A wide-field clinical photograph of a skin lesion; Fitzpatrick phototype II; the chart records a prior melanoma; a female subject roughly 75 years of age:
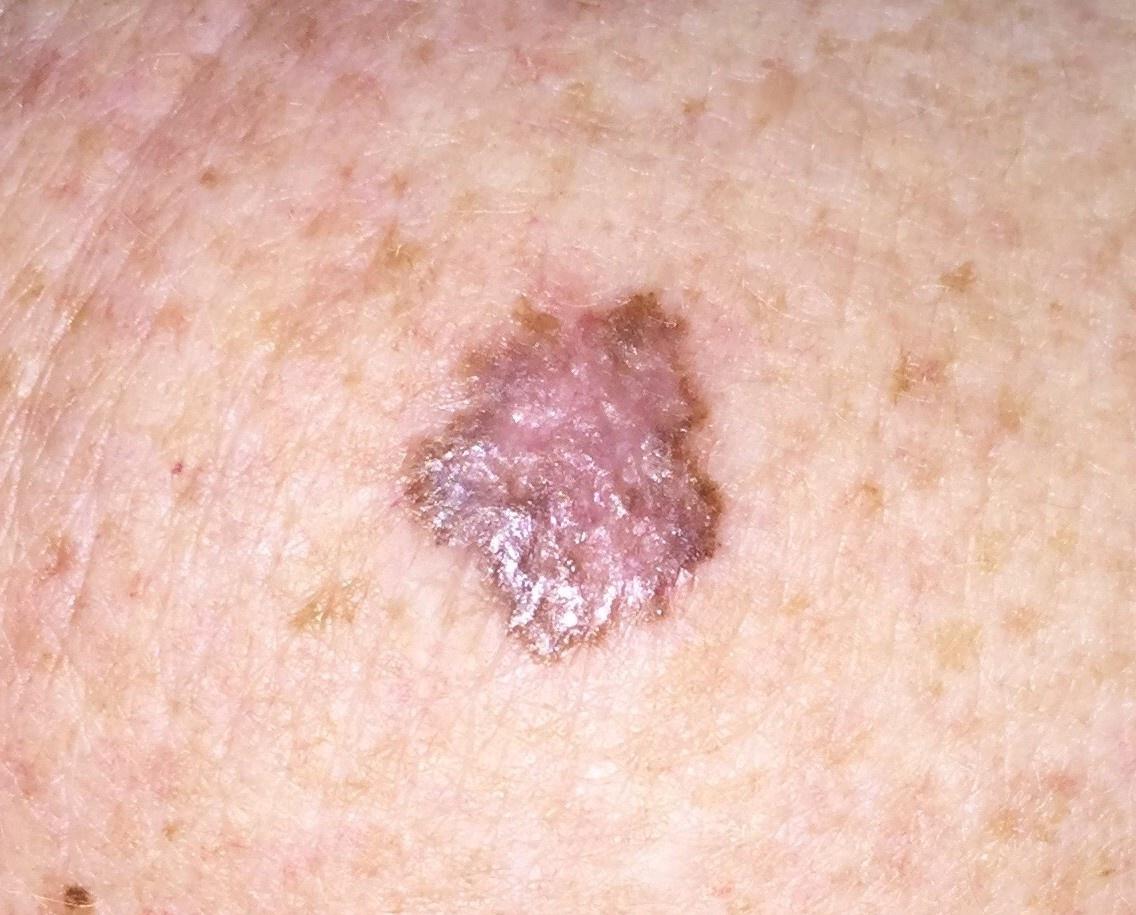{
  "lesion_location": {
    "region": "an upper extremity"
  },
  "diagnosis": {
    "name": "Melanoma",
    "malignancy": "malignant",
    "confirmation": "histopathology"
  }
}